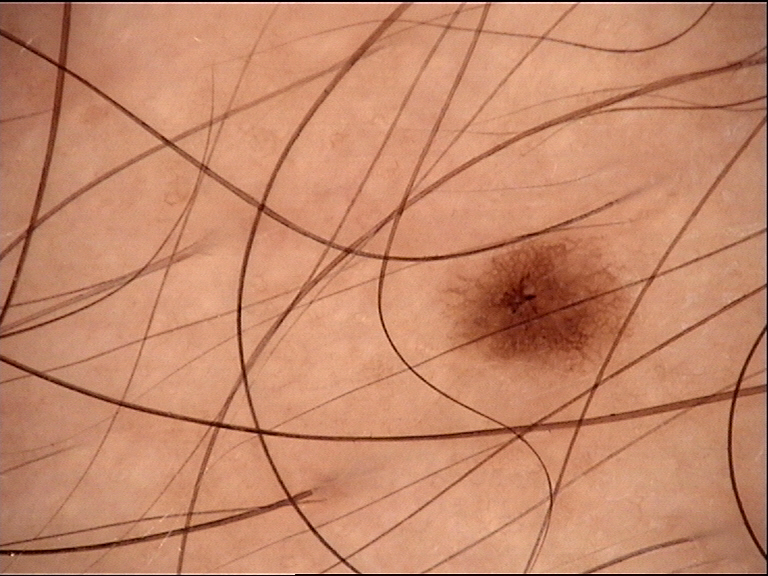Findings:
- image type — dermoscopy
- assessment — dysplastic junctional nevus (expert consensus)